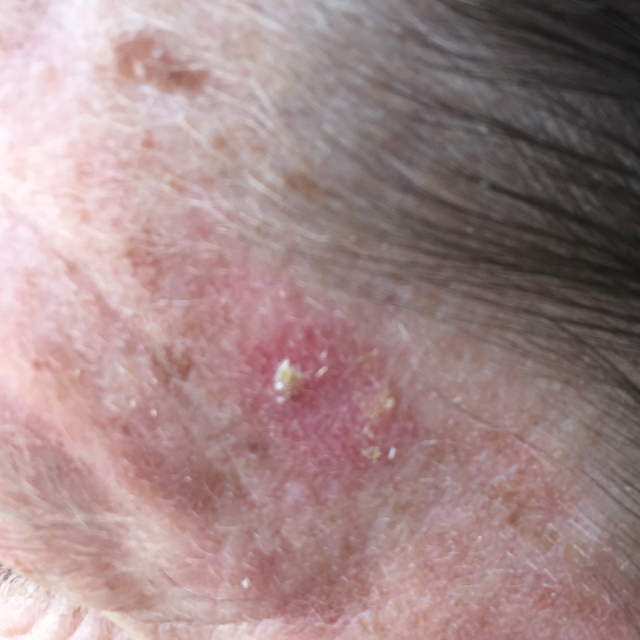Summary: A clinical photograph showing a skin lesion. A patient age 54. The lesion is located on the face. The patient reports that the lesion itches. Conclusion: The clinical impression was an actinic keratosis.